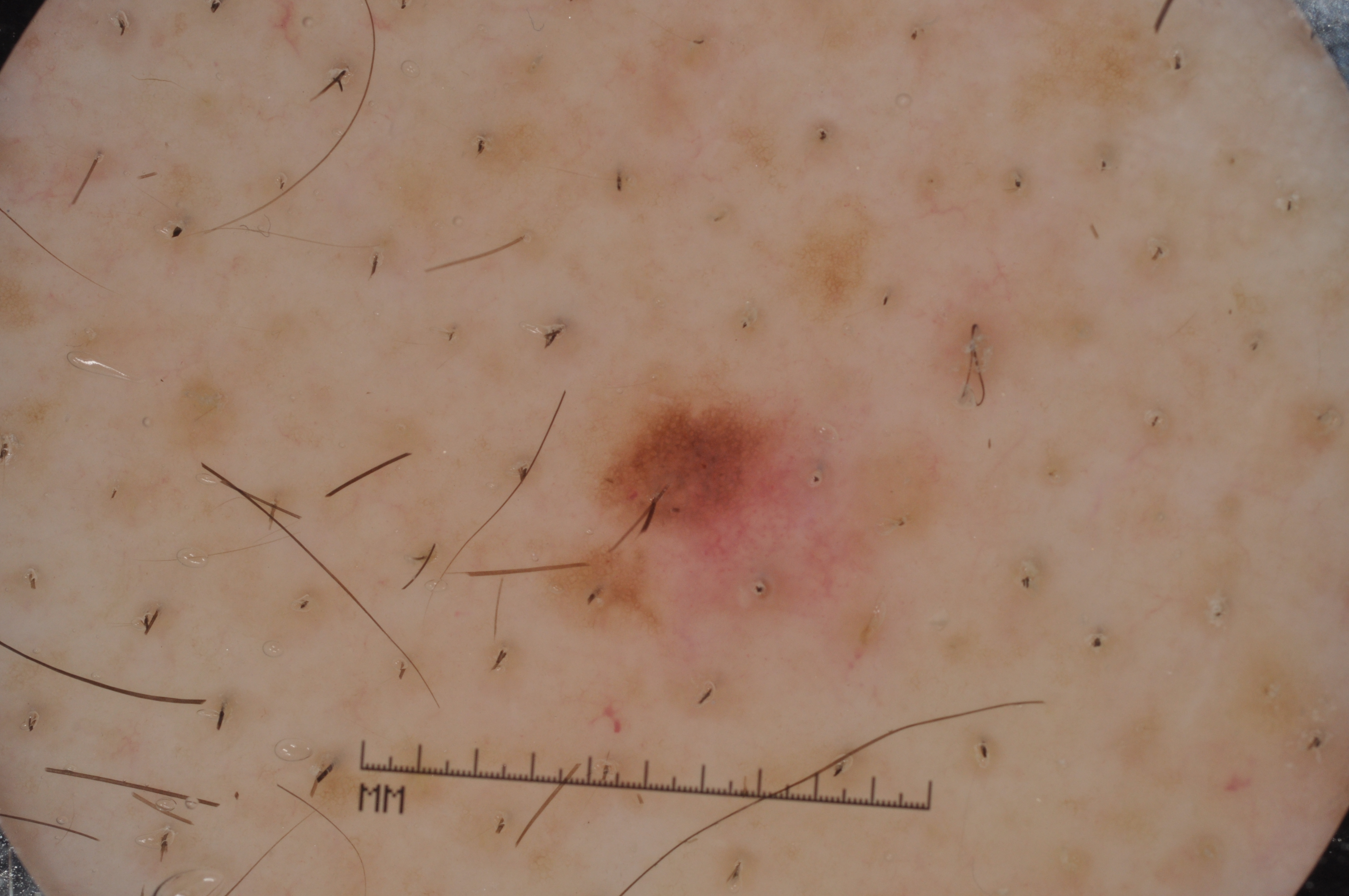A dermoscopic image of a skin lesion. A male patient, about 65 years old. In (x1, y1, x2, y2) order, the visible lesion spans [569,378,927,616]. The lesion is small relative to the field of view. Dermoscopic examination shows pigment network, with no negative network, milia-like cysts, or streaks. The clinical diagnosis was a melanocytic nevus, a benign lesion.